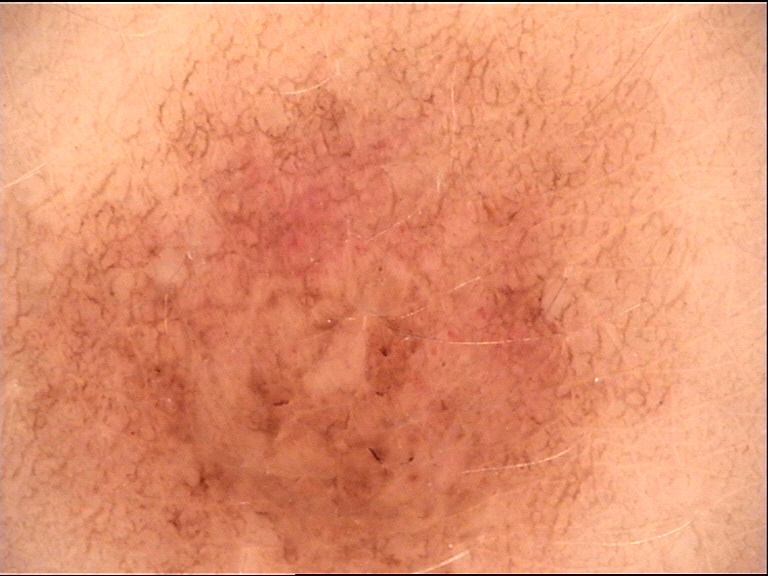| field | value |
|---|---|
| modality | dermatoscopy |
| lesion type | banal |
| class | compound nevus (expert consensus) |